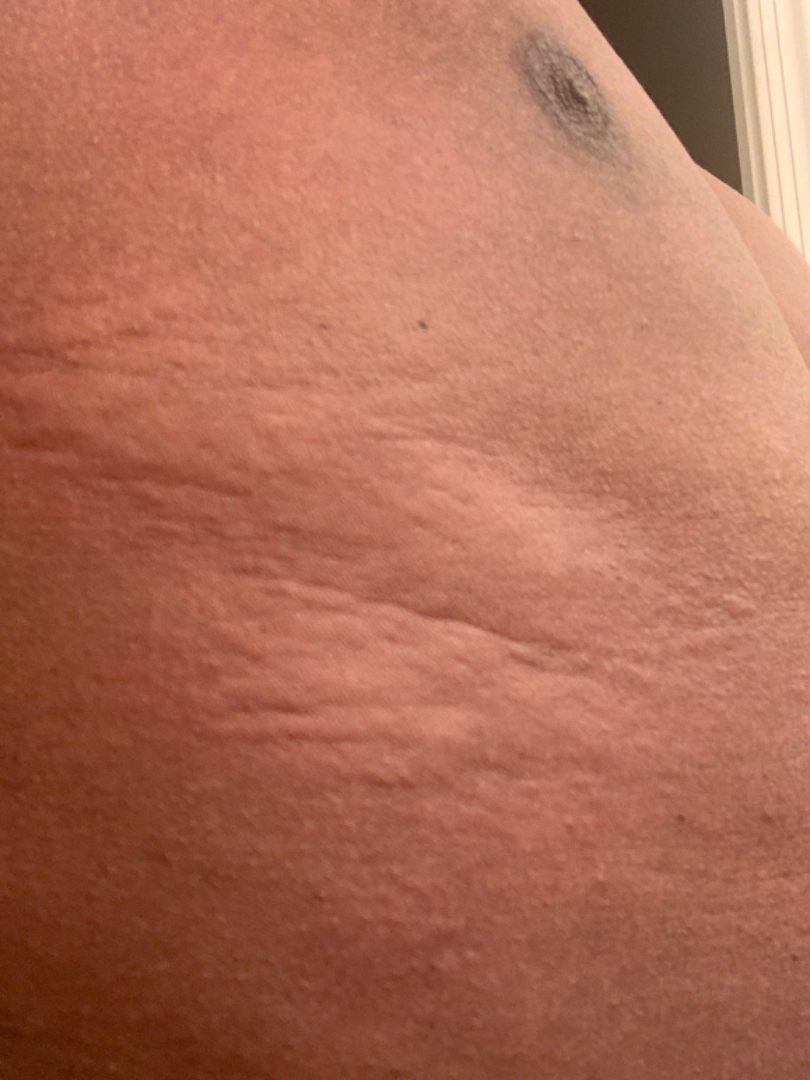Associated systemic symptoms include joint pain. The condition has been present for about one day. Located on the front of the torso and leg. The contributor is a male aged 30–39. Self-categorized by the patient as a growth or mole. An image taken at an angle. The lesion is described as raised or bumpy. Three independent reviewers: the favored diagnosis is Urticaria; a more distant consideration is Allergic Contact Dermatitis.